The contributor is 40–49, female. The photograph was taken at a distance:
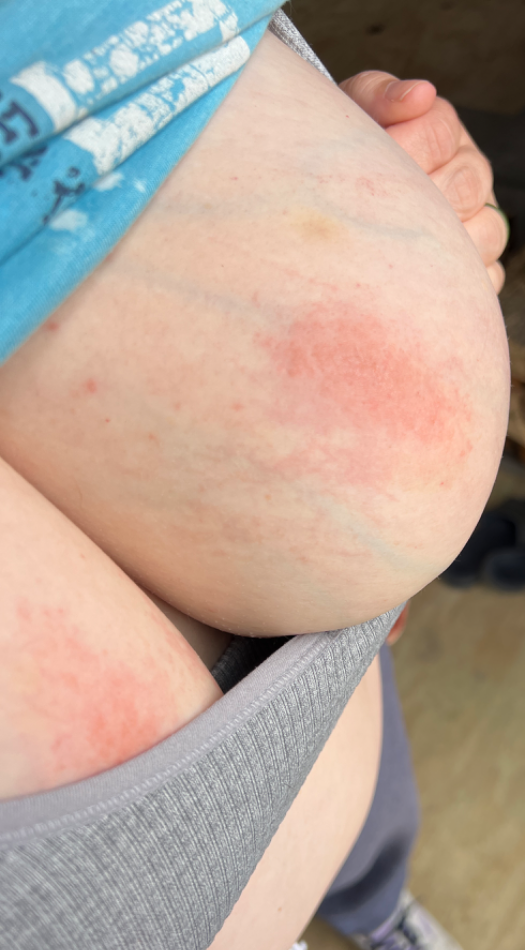On dermatologist assessment of the image: the differential includes Eczema and Allergic Contact Dermatitis, with no clear leading consideration; less probable is Psoriasis.